Dermoscopy of a skin lesion.
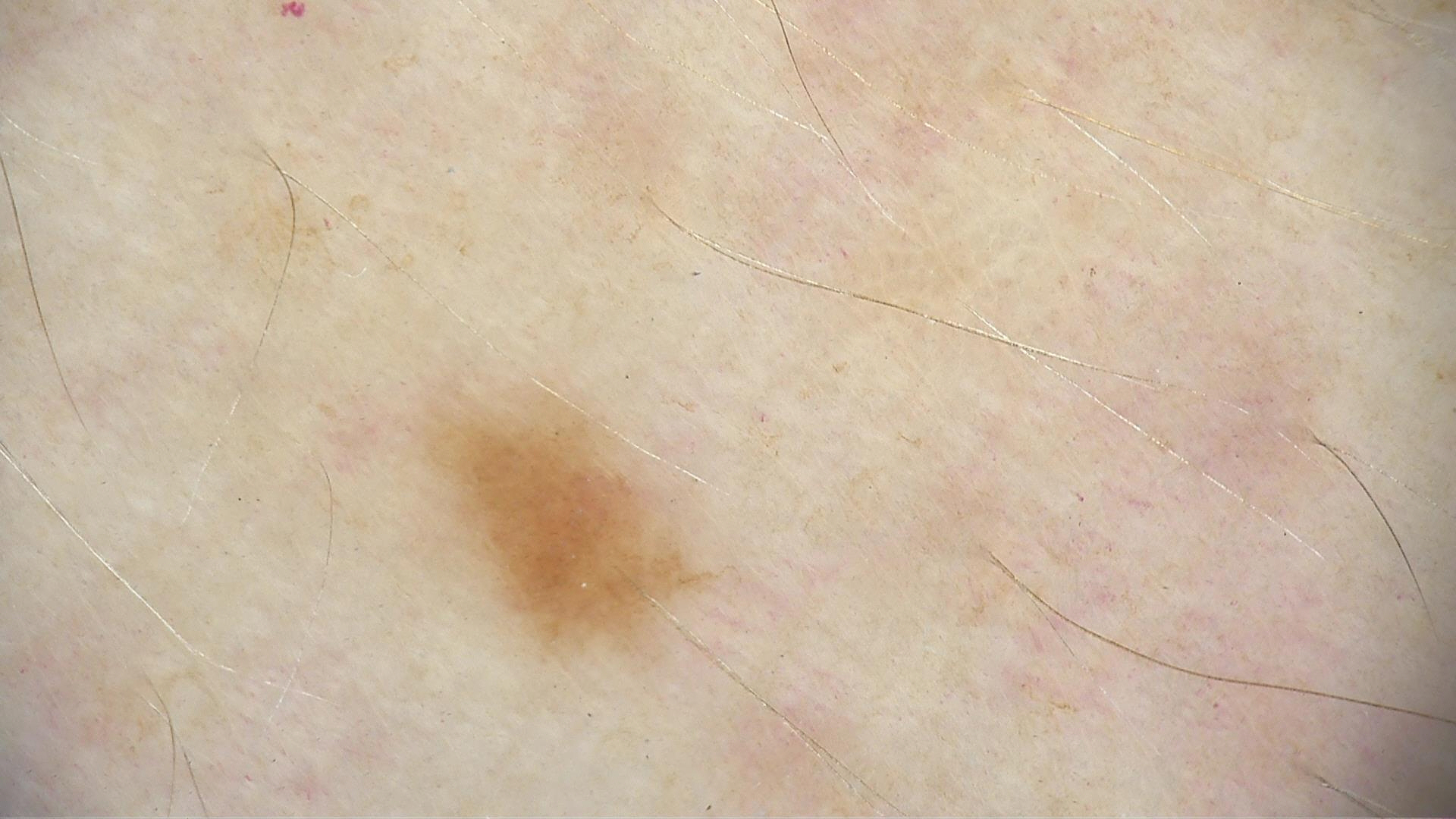<lesion>
  <diagnosis>
    <name>junctional nevus</name>
    <code>jb</code>
    <malignancy>benign</malignancy>
    <super_class>melanocytic</super_class>
    <confirmation>expert consensus</confirmation>
  </diagnosis>
</lesion>